A dermoscopic photograph of a skin lesion.
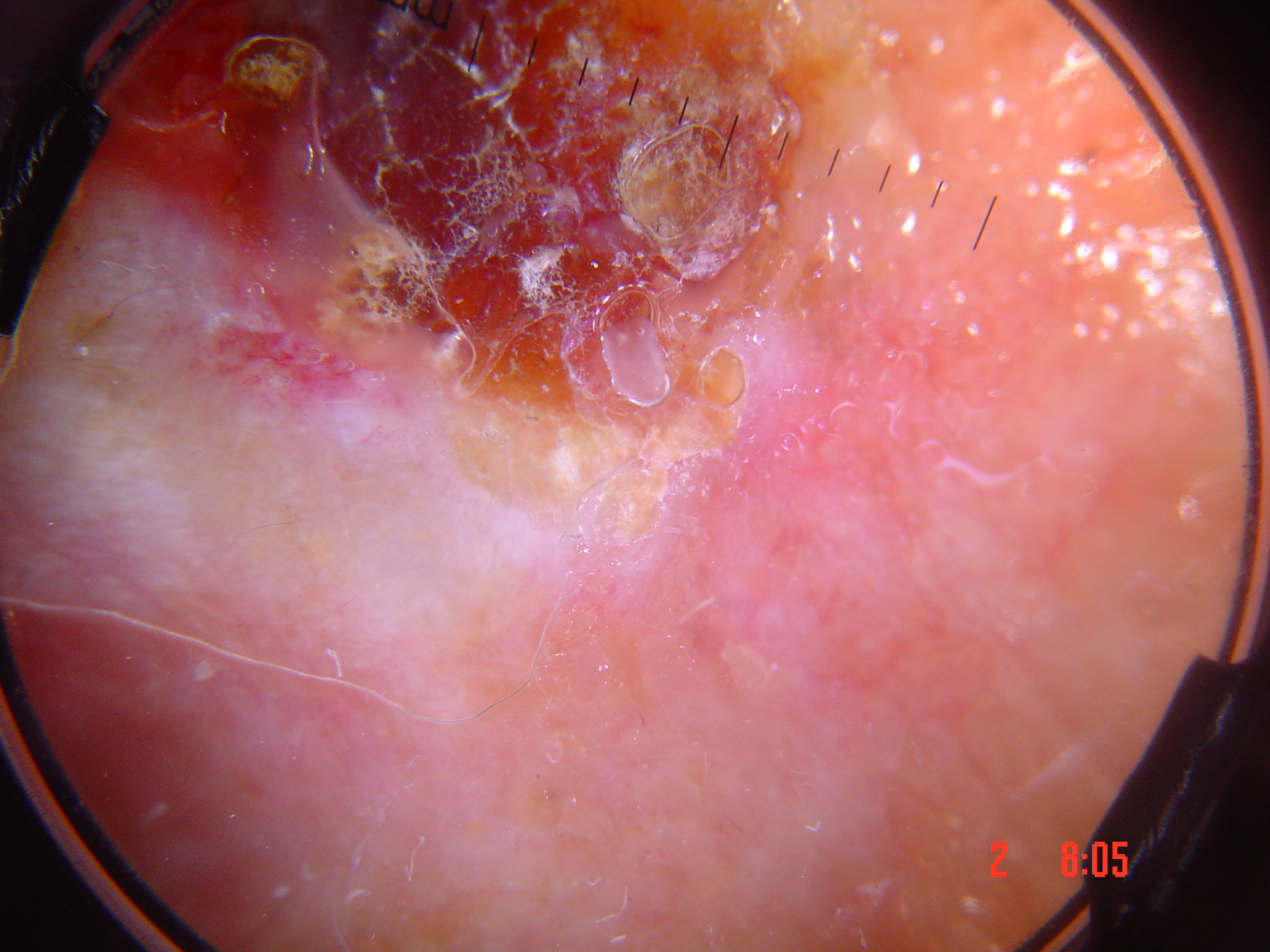Histopathology confirmed a keratinocytic lesion — a squamous cell carcinoma.